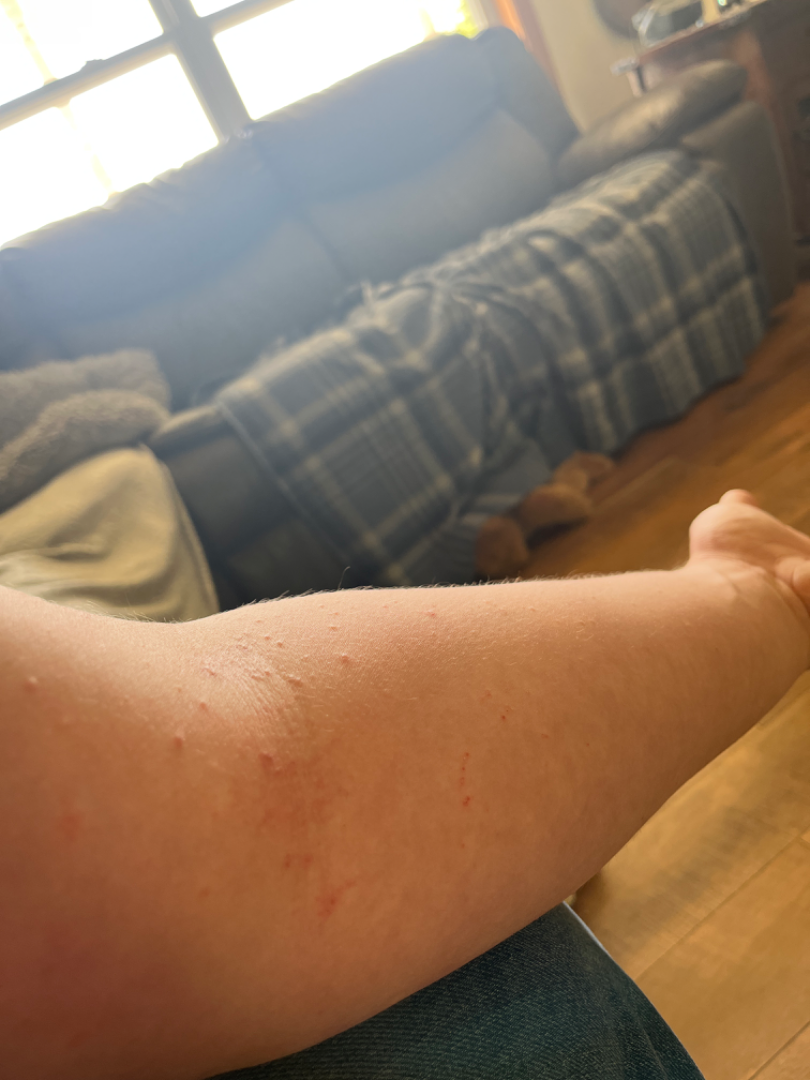- anatomic site — arm and head or neck
- photo taken — at an angle
- contributor — male, age 18–29
- diagnostic considerations — most likely Eczema; lower on the differential is Irritant Contact Dermatitis; less likely is Insect Bite; less probable is Allergic Contact Dermatitis